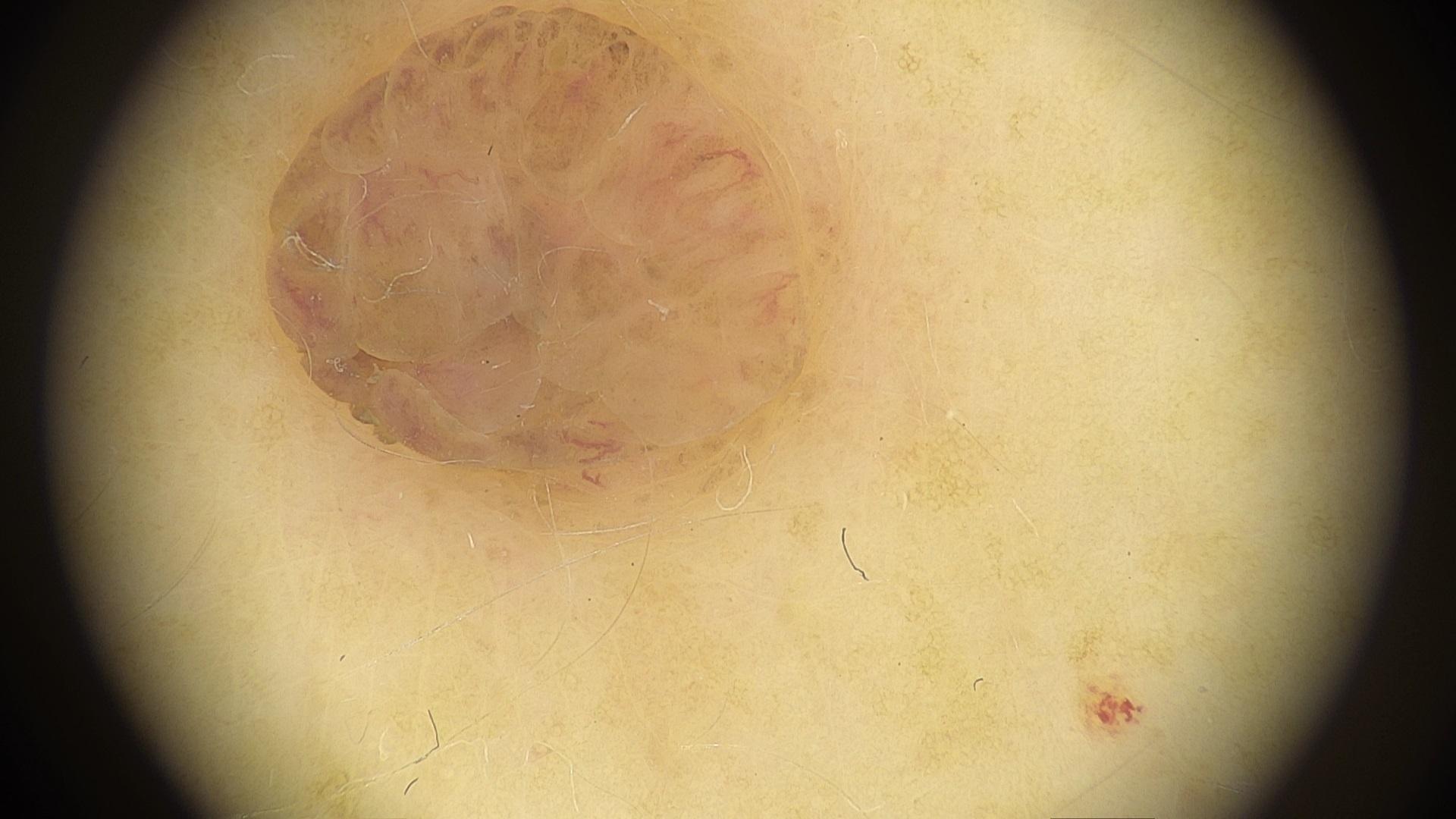A female subject approximately 50 years of age. Contact-polarized dermoscopy of a skin lesion. The patient is Fitzpatrick phototype II. The diagnostic impression was a melanocytic lesion — a nevus.